The patient reports immunosuppression, a prior organ transplant, and no sunbed use. Collected as part of a research study, without a referral diagnosis. The patient says their skin reddens painfully with sun exposure. The patient describes having a moderate number of moles: 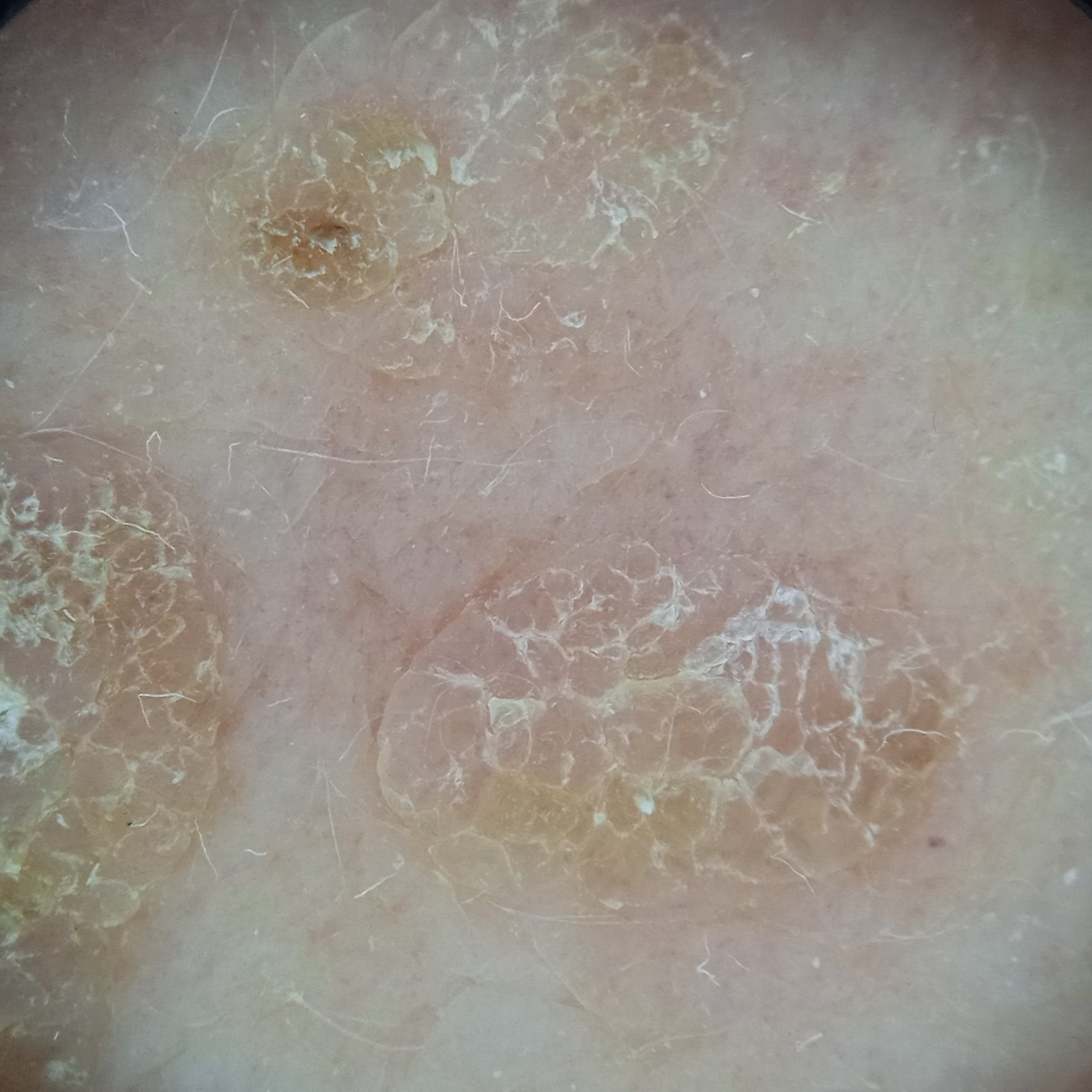The lesion is about 10.6 mm across. The lesion was assessed as a seborrheic keratosis.